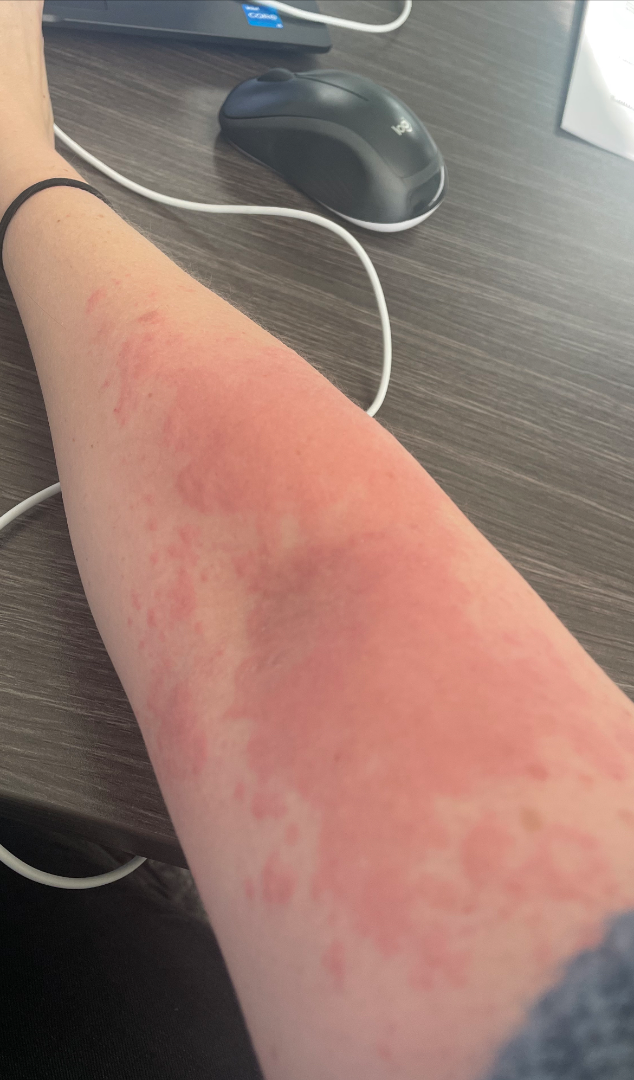The patient is 30–39, female.
Texture is reported as rough or flaky and raised or bumpy.
Reported lesion symptoms include bothersome appearance, enlargement and itching.
The photograph is a close-up of the affected area.
The affected area is the arm.
Present for less than one week.
The patient considered this skin that appeared healthy to them.
The favored diagnosis is Hypersensitivity; also raised was Irritant Contact Dermatitis.